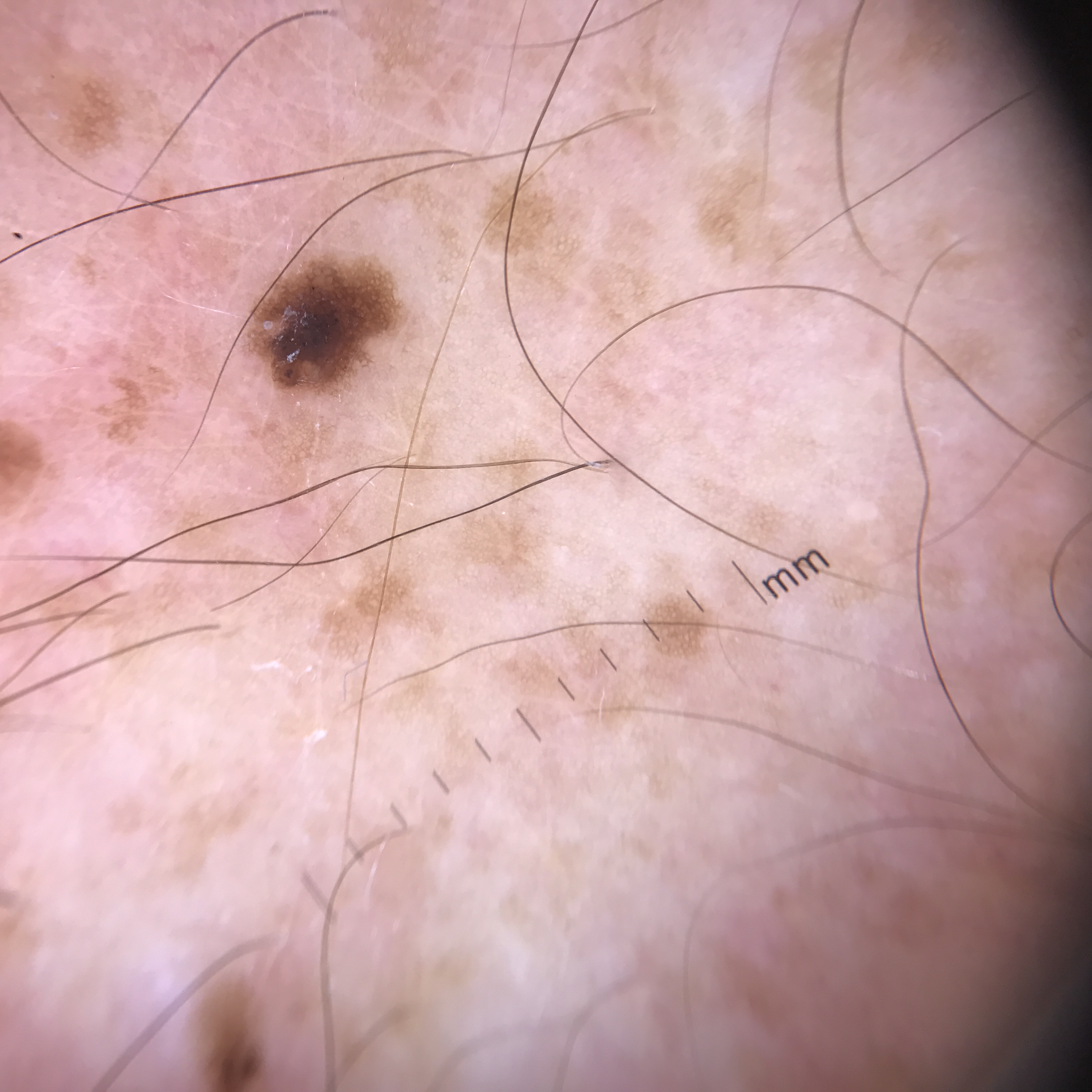{
  "image": "dermatoscopy",
  "lesion_type": {
    "main_class": "banal",
    "pattern": "junctional"
  },
  "diagnosis": {
    "name": "junctional nevus",
    "code": "jb",
    "malignancy": "benign",
    "super_class": "melanocytic",
    "confirmation": "expert consensus"
  }
}